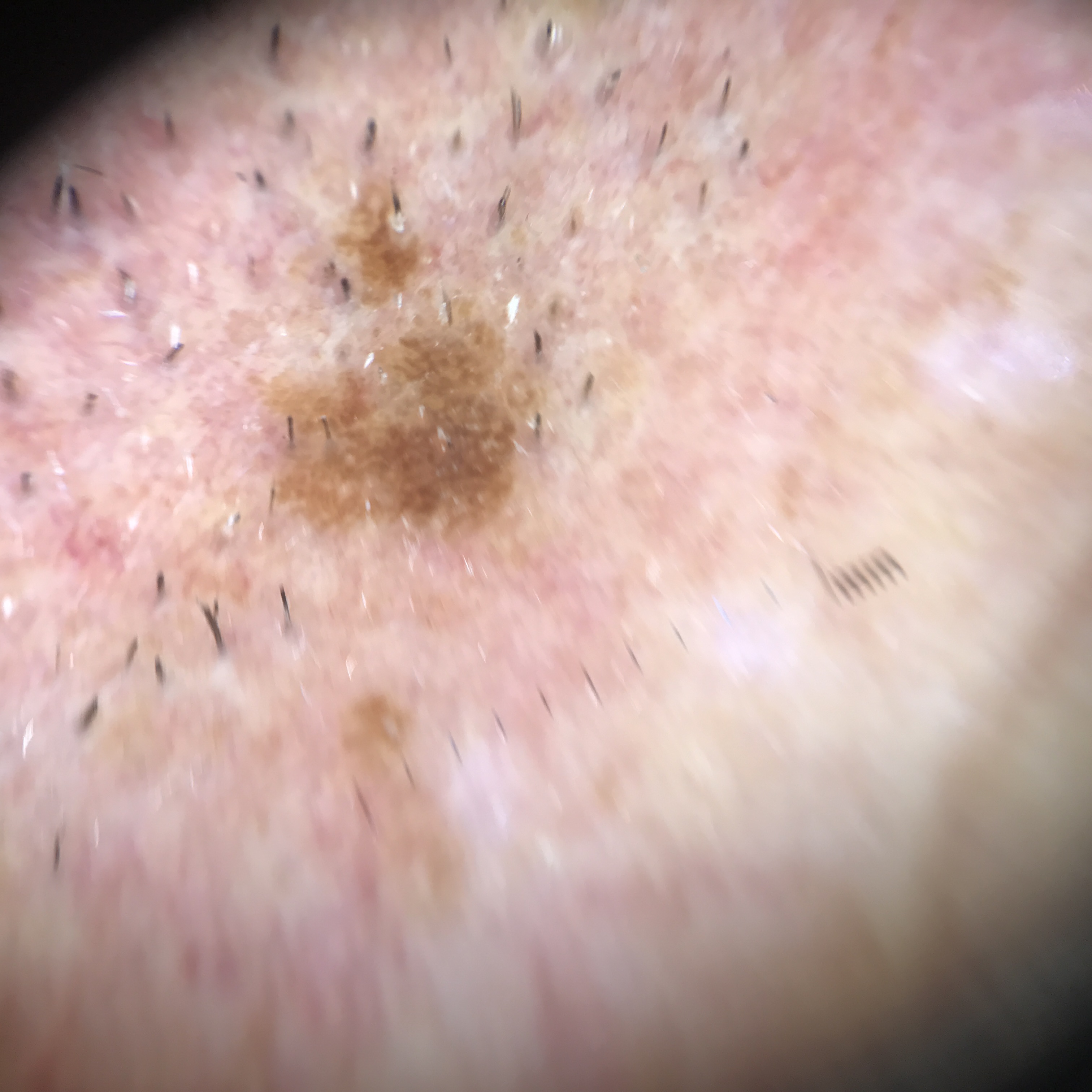Conclusion: The diagnosis was a solar lentigo.